The affected area is the front of the torso. The patient is 18–29, female. This image was taken at a distance — 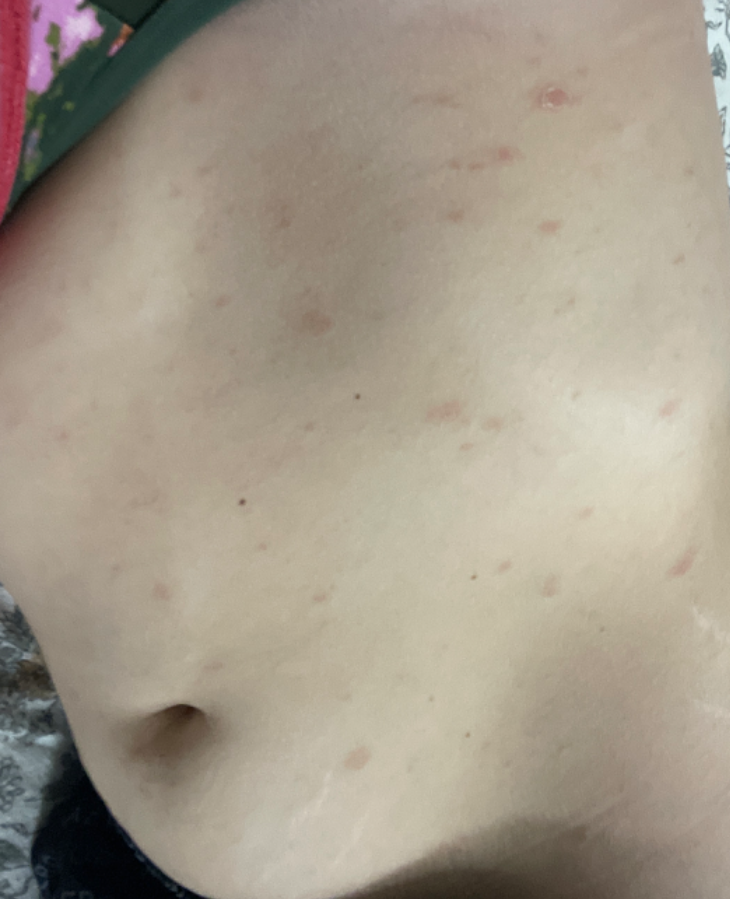Notes:
– dermatologist impression — the differential includes Pityriasis rosea, Acute and chronic dermatitis and Pityriasis lichenoides, with no clear leading consideration